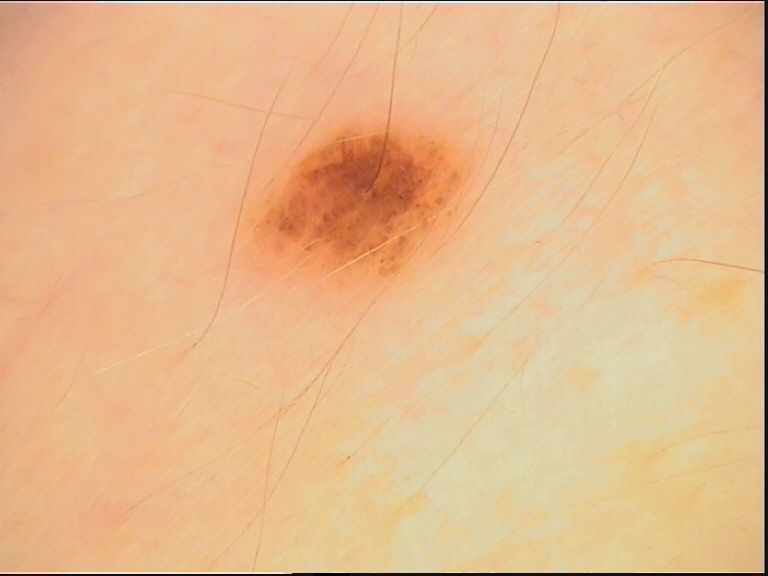image: dermoscopy, subtype: banal, diagnostic label: compound nevus (expert consensus).